Located on the arm; the photo was captured at an angle.
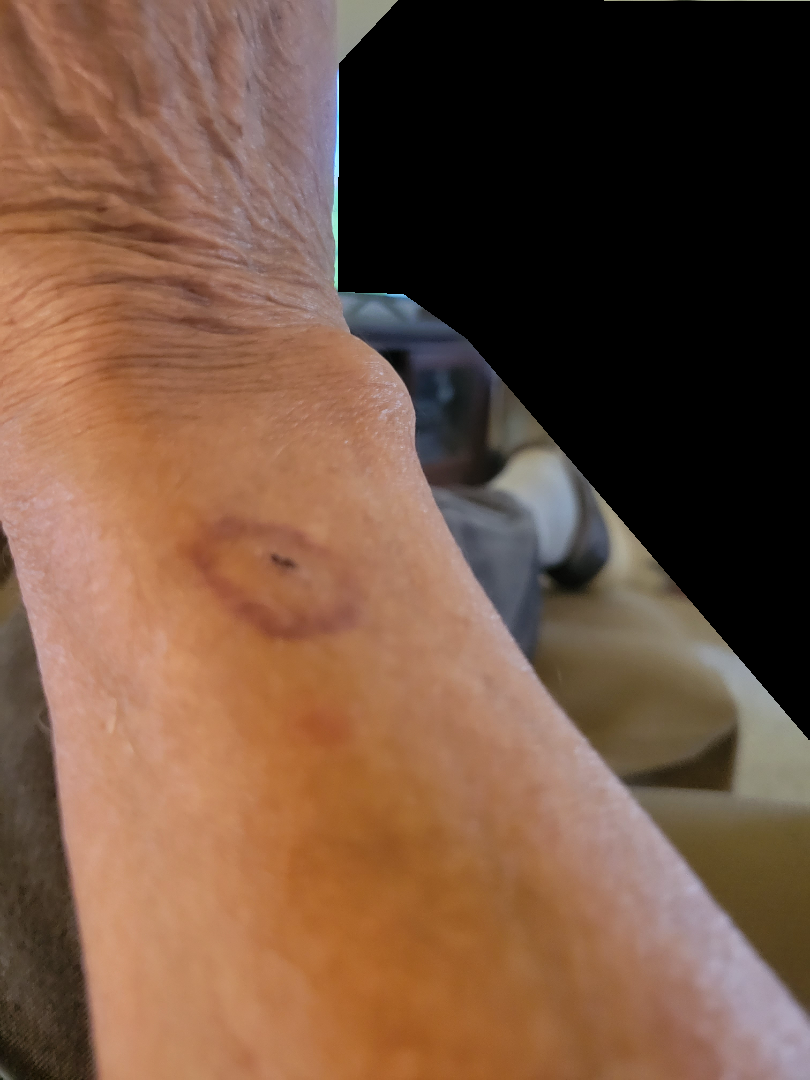  assessment: could not be assessed